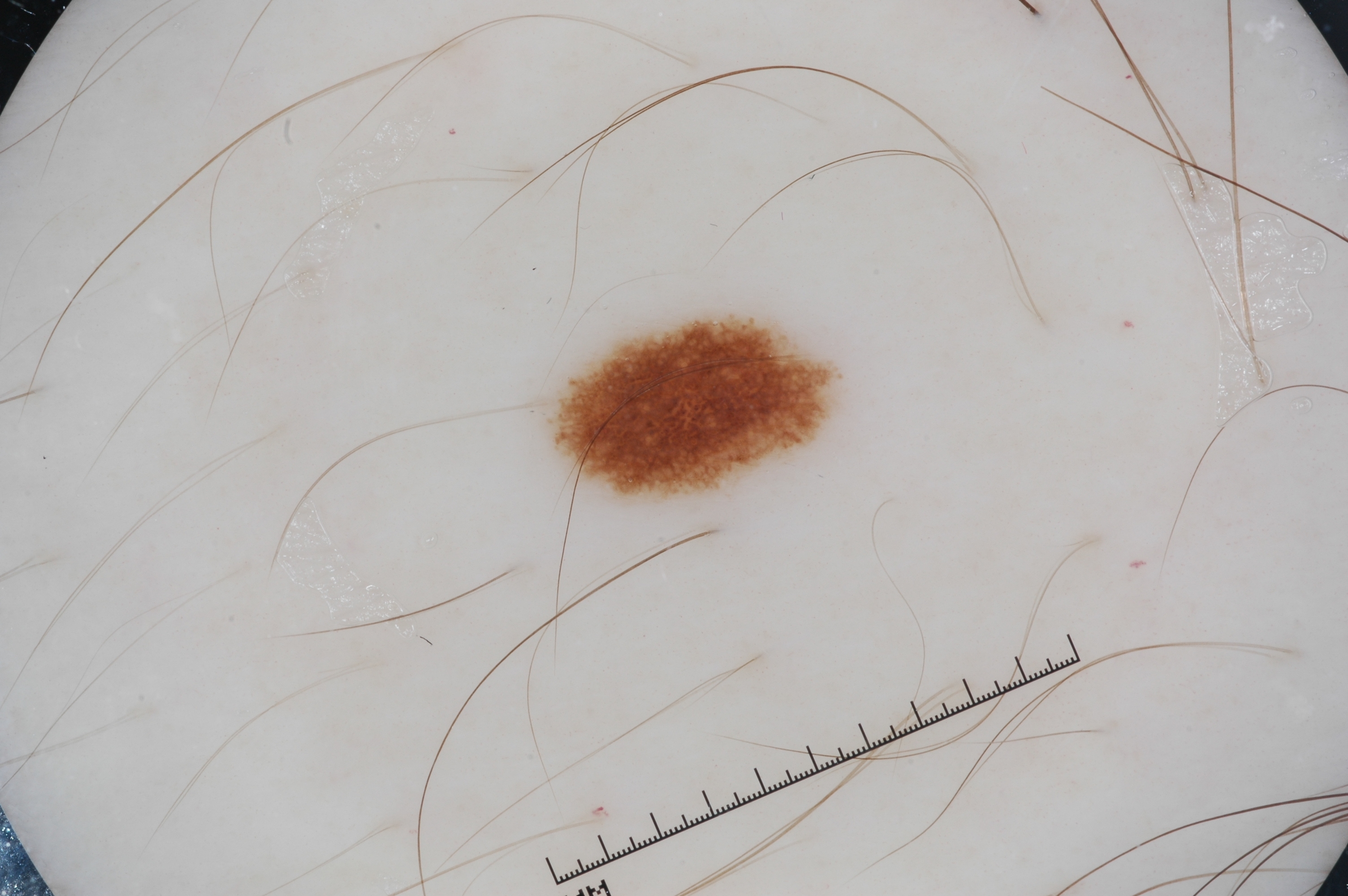Q: Who is the patient?
A: male, roughly 25 years of age
Q: How was this image acquired?
A: dermoscopic image
Q: What does dermoscopy show?
A: pigment network and negative network; absent: streaks and milia-like cysts
Q: What is the lesion's bounding box?
A: 544, 310, 847, 509
Q: How large is the lesion within the image?
A: ~4% of the field
Q: What is this lesion?
A: a melanocytic nevus